The arm is involved. The photograph is a close-up of the affected area. The subject is a female aged 50–59.
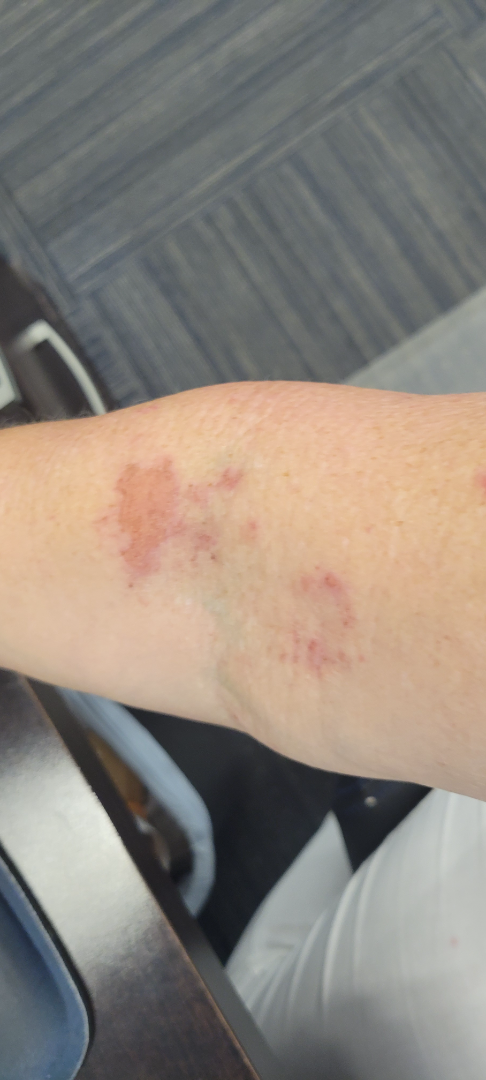Reviewed remotely by one dermatologist: the leading consideration is Allergic Contact Dermatitis; an alternative is Eczema; less probable is Tinea.